The photo was captured at an angle:
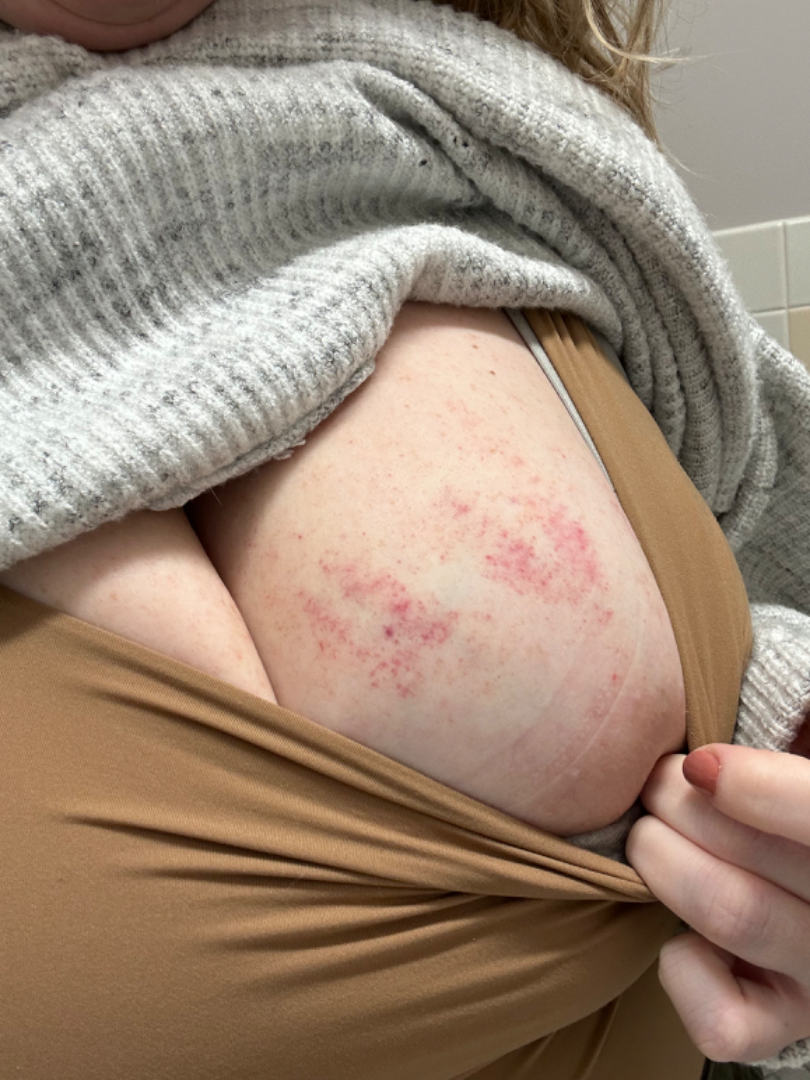The reviewing clinician's impression was: ecchymoses (leading).